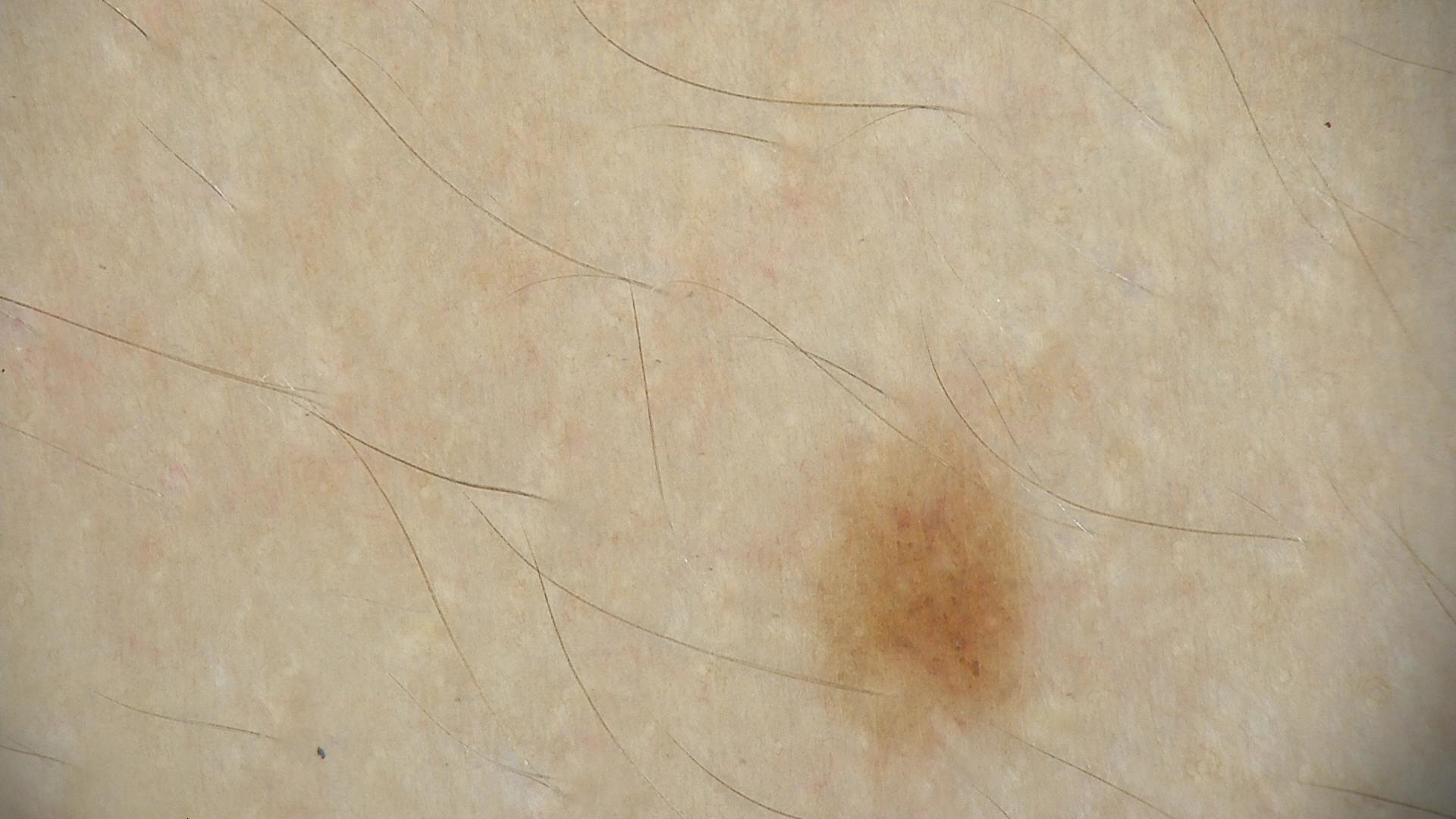- diagnosis — dysplastic junctional nevus (expert consensus)